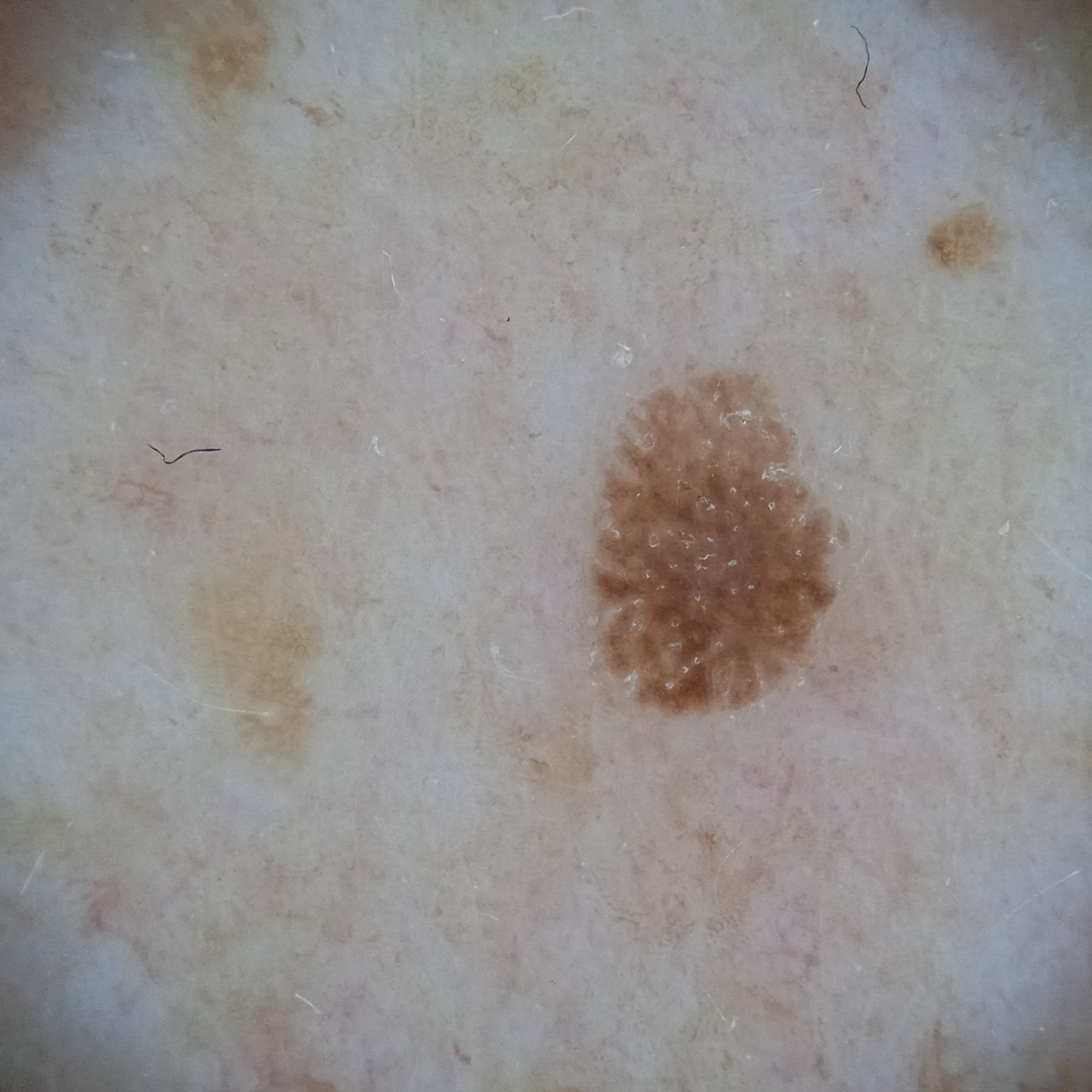<skin_lesion>
<sun_reaction>skin reddens with sun exposure</sun_reaction>
<image>dermatoscopic image</image>
<referral>research study (no referral diagnosis)</referral>
<patient>
<age>62</age>
<sex>male</sex>
</patient>
<mole_burden>few melanocytic nevi overall</mole_burden>
<lesion_location>the back</lesion_location>
<lesion_size>
<diameter_mm>4.3</diameter_mm>
</lesion_size>
<diagnosis>
<name>seborrheic keratosis</name>
<malignancy>benign</malignancy>
</diagnosis>
</skin_lesion>